The affected area is the arm and leg; the photo was captured at an angle — 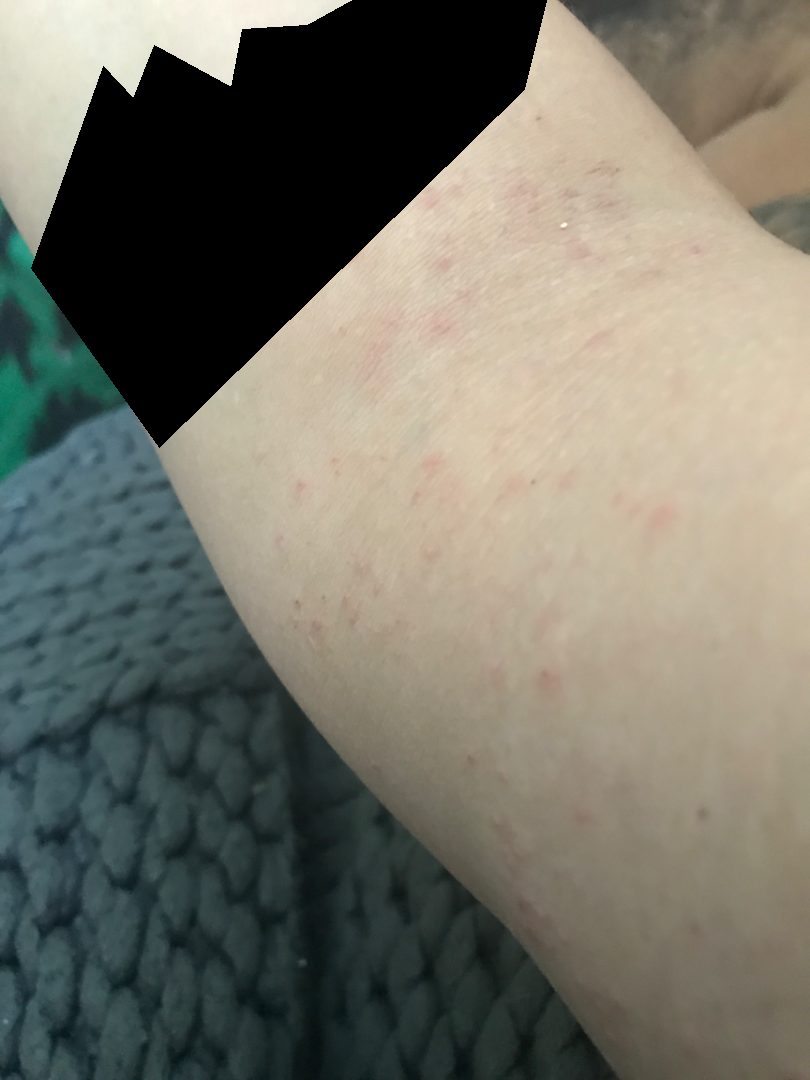Most consistent with Eczema.